The photo was captured at a distance — 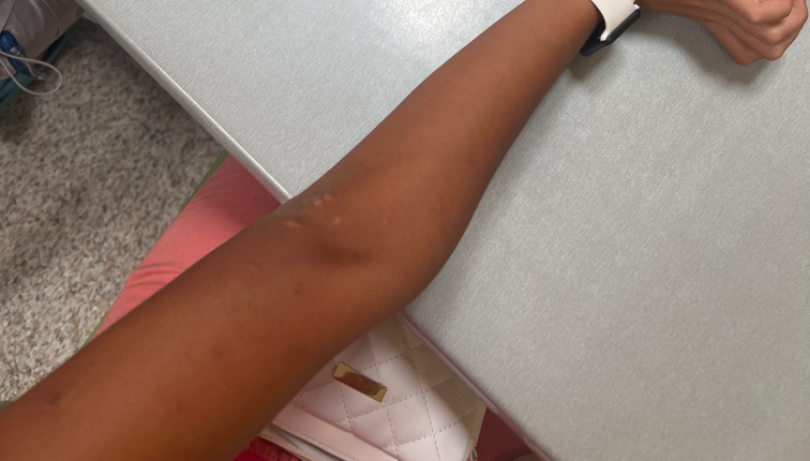Impression:
The case was indeterminate on photographic review.